A dermoscopic image of a skin lesion.
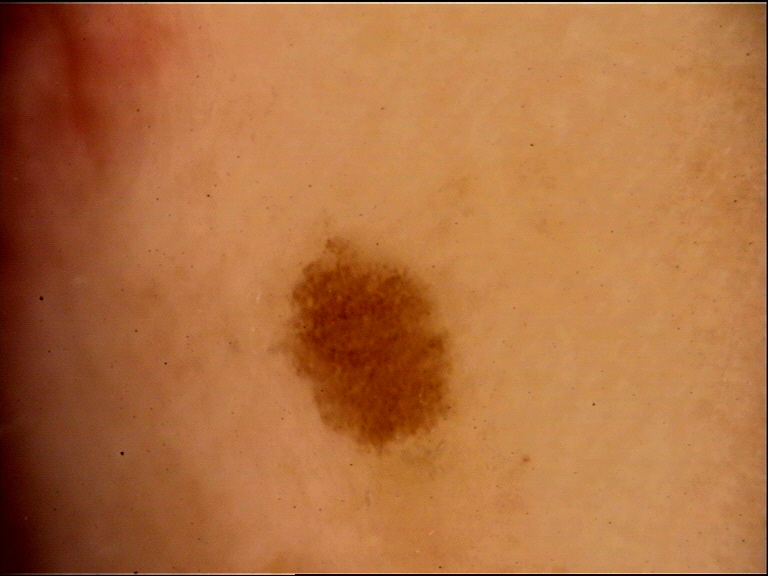The diagnostic label was a dysplastic junctional nevus.